The lesion involves the arm · male subject, age 40–49 · an image taken at a distance.
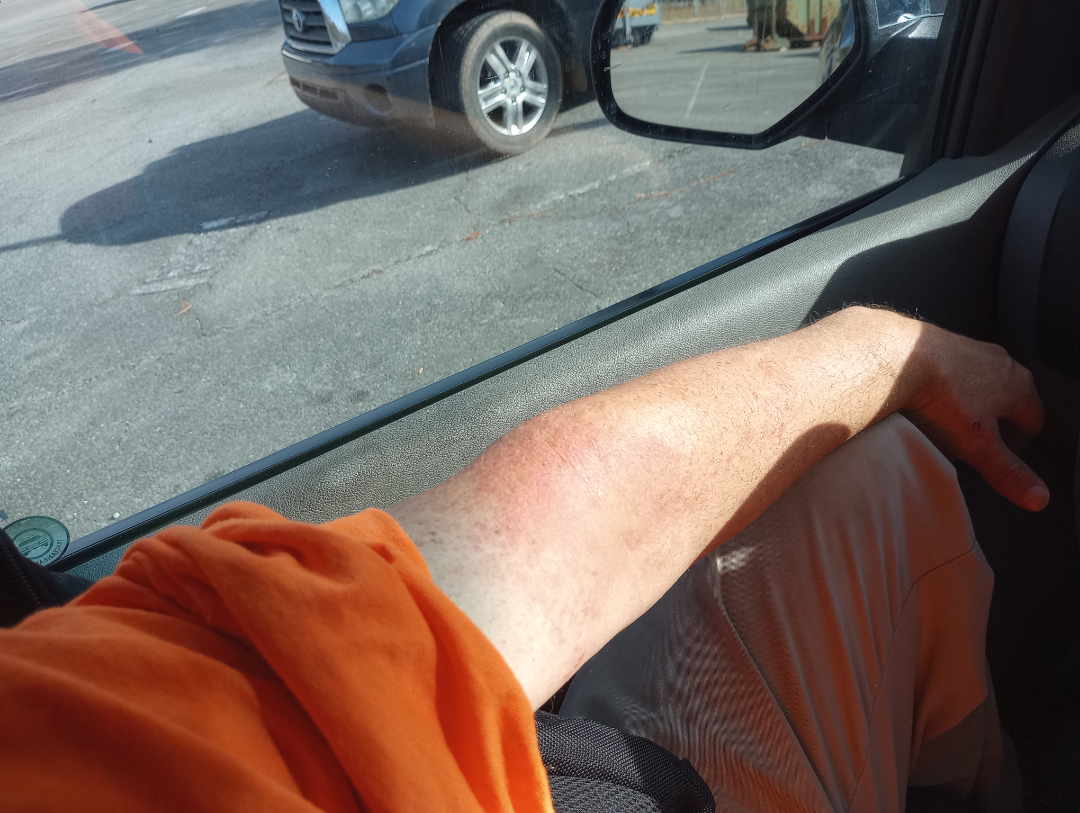The lesion is described as raised or bumpy.
Self-categorized by the patient as a rash.
Fitzpatrick skin type II.
No constitutional symptoms were reported.
Symptoms reported: itching.
The condition has been present for one to four weeks.
On photographic review by a dermatologist, most consistent with Eczema; an alternative is Psoriasis; also on the differential is Allergic Contact Dermatitis.